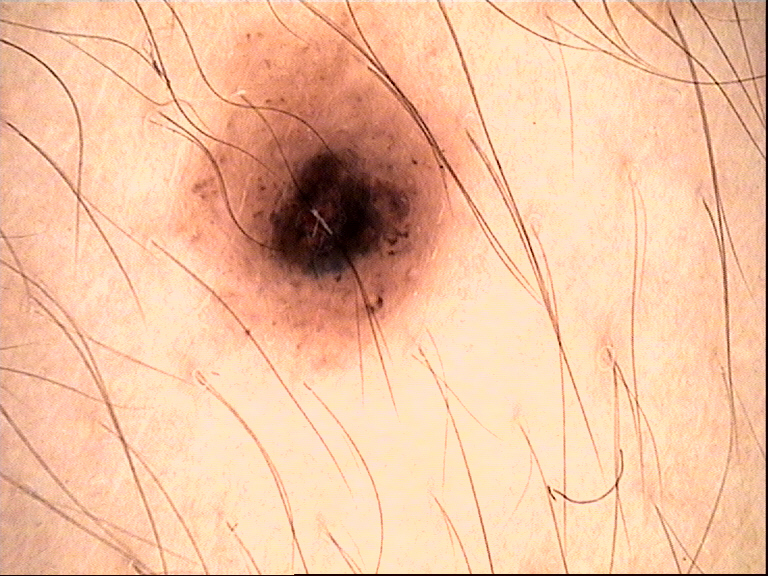Impression: The diagnosis was a dysplastic junctional nevus.